The photograph is a close-up of the affected area: 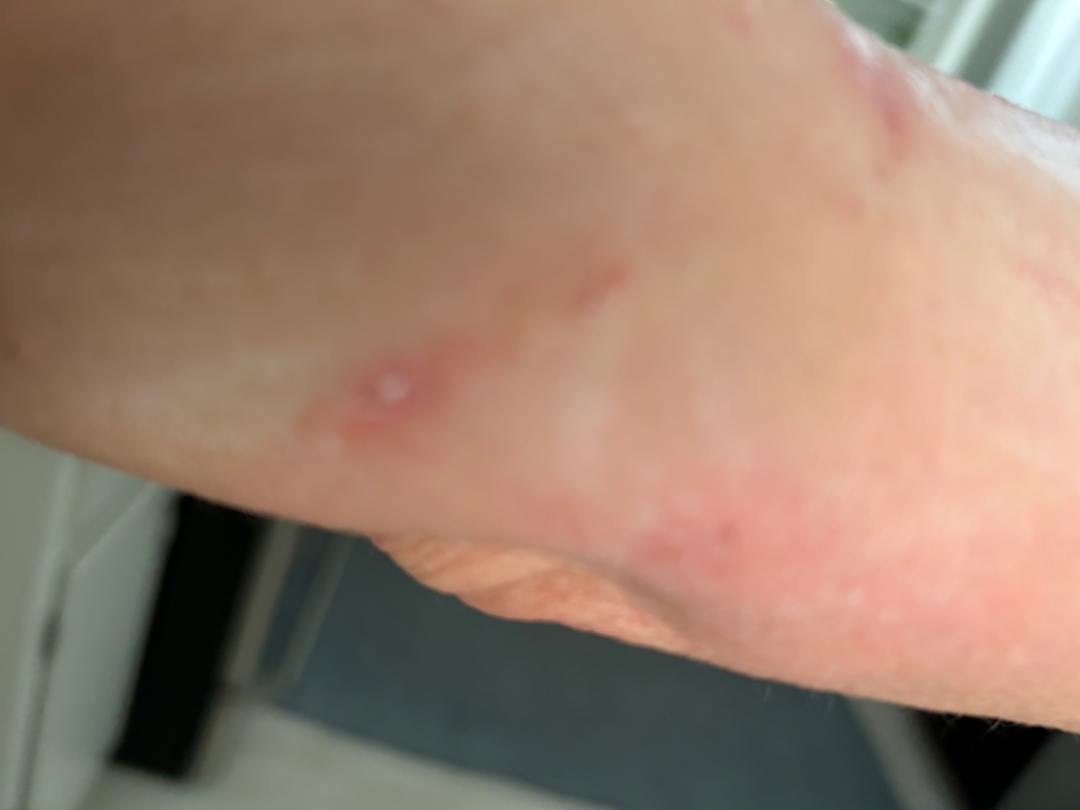The skin condition could not be confidently assessed from this image.